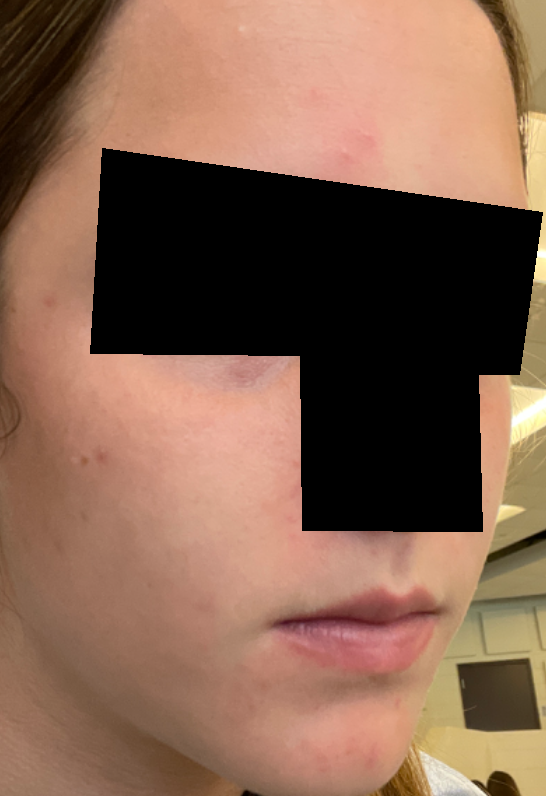Q: How long has this been present?
A: less than one week
Q: Reported symptoms?
A: enlargement
Q: Texture?
A: raised or bumpy
Q: How was the photo taken?
A: at an angle
Q: Patient's own categorization?
A: a rash
Q: Any systemic symptoms?
A: none reported
Q: What is the dermatologist's impression?
A: favoring Acne